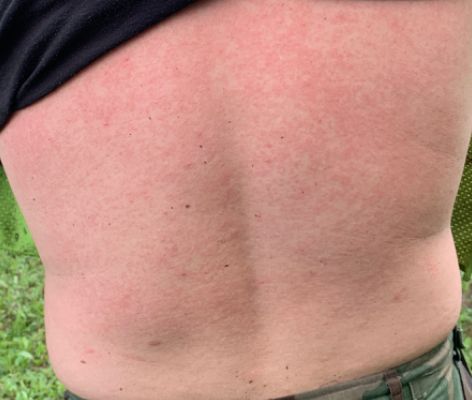Findings:
The dermatologist could not determine a likely condition from the photograph alone.
Background:
The patient reports the condition has been present for about one day. Located on the back of the torso. This image was taken at a distance. The patient reports the lesion is raised or bumpy.